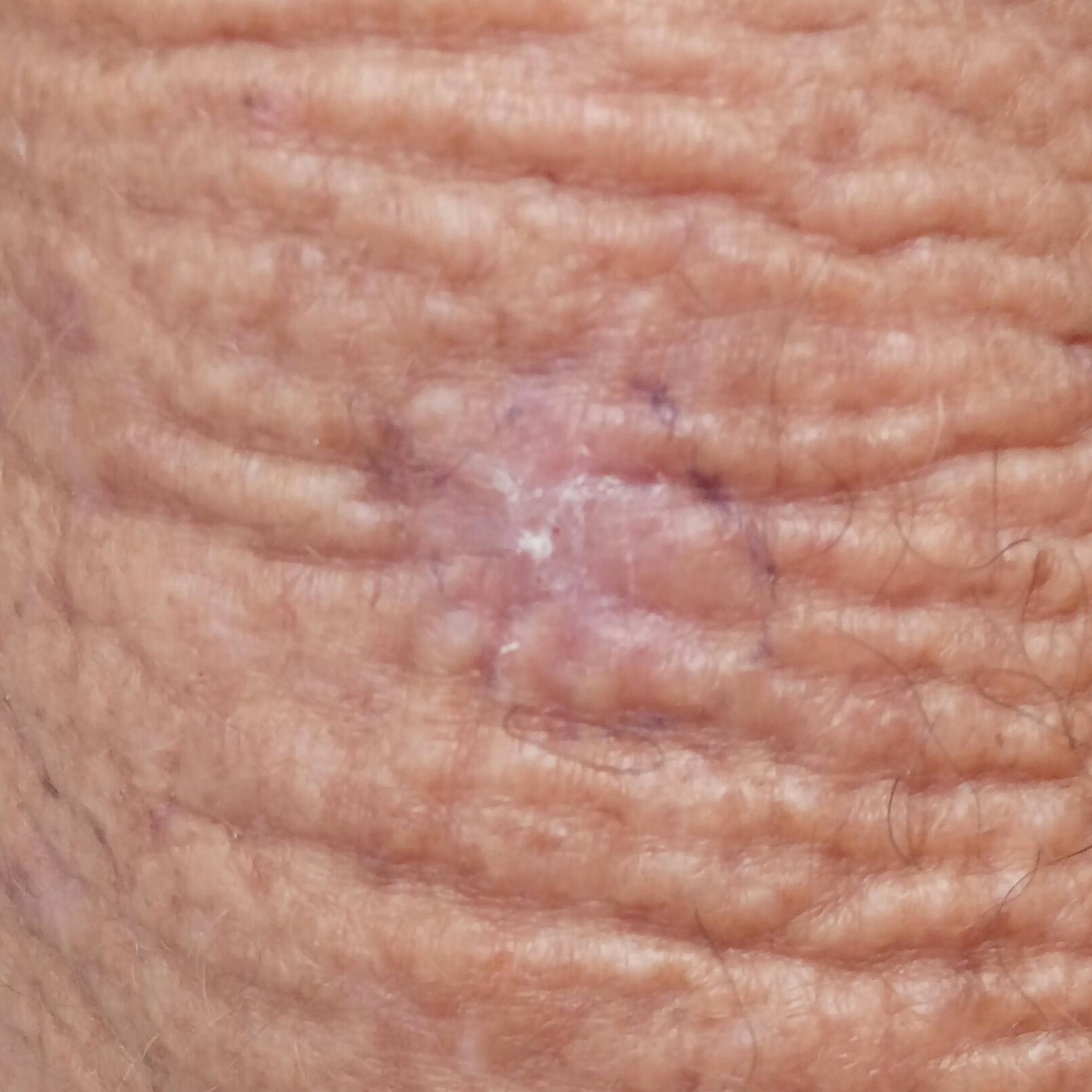Summary: The lesion was found on a forearm. The patient reports that the lesion has not bled and does not hurt. Conclusion: Consistent with an actinic keratosis.